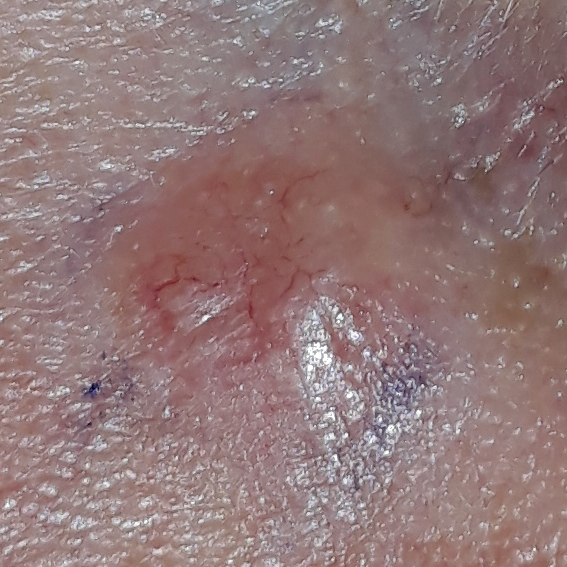The chart notes prior malignancy (patient or family), alcohol use, pesticide exposure, no tobacco use, and no prior skin cancer (patient or family). A female patient in their 40s. A clinical close-up photograph of a skin lesion. Recorded as Fitzpatrick phototype II. Located on the nose. The lesion measures approximately 7 × 7 mm. Per patient report, the lesion is elevated. Confirmed on histopathology as a basal cell carcinoma.